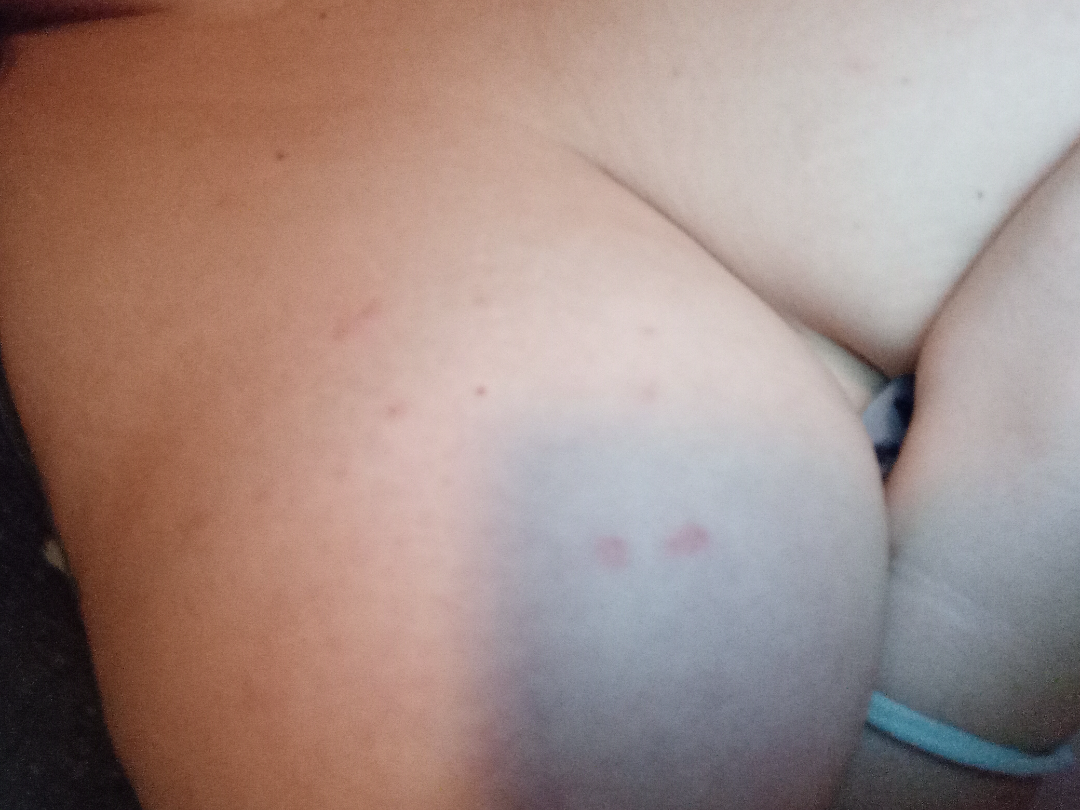• assessment — not assessable
• subject — female, age 30–39
• shot type — close-up
• self-categorized as — a rash
• patient-reported symptoms — burning and itching
• onset — less than one week
• site — back of the torso and front of the torso
• skin tone — Fitzpatrick skin type I
• surface texture — fluid-filled, rough or flaky and raised or bumpy